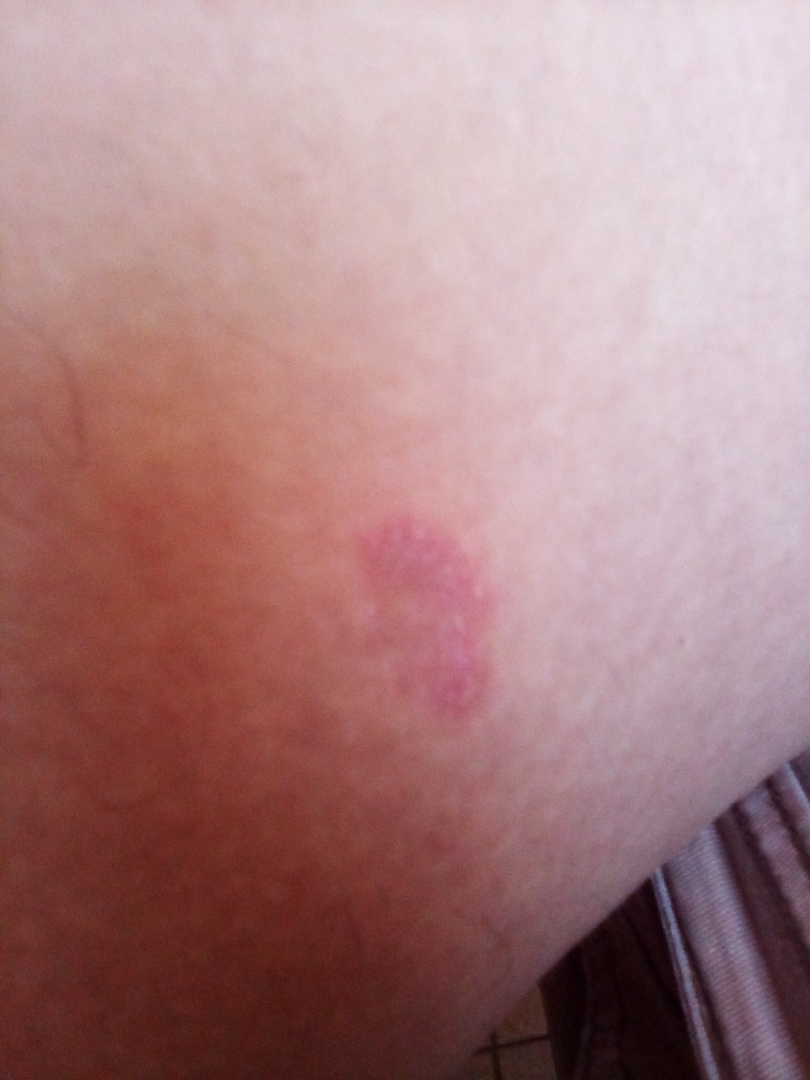site = leg | skin tone = Fitzpatrick skin type II | lesion symptoms = enlargement and itching | lesion texture = raised or bumpy and rough or flaky | view = close-up | symptom duration = one to four weeks | subject = male, age 30–39 | dermatologist impression = Tinea and Eczema were each considered, in no particular order.